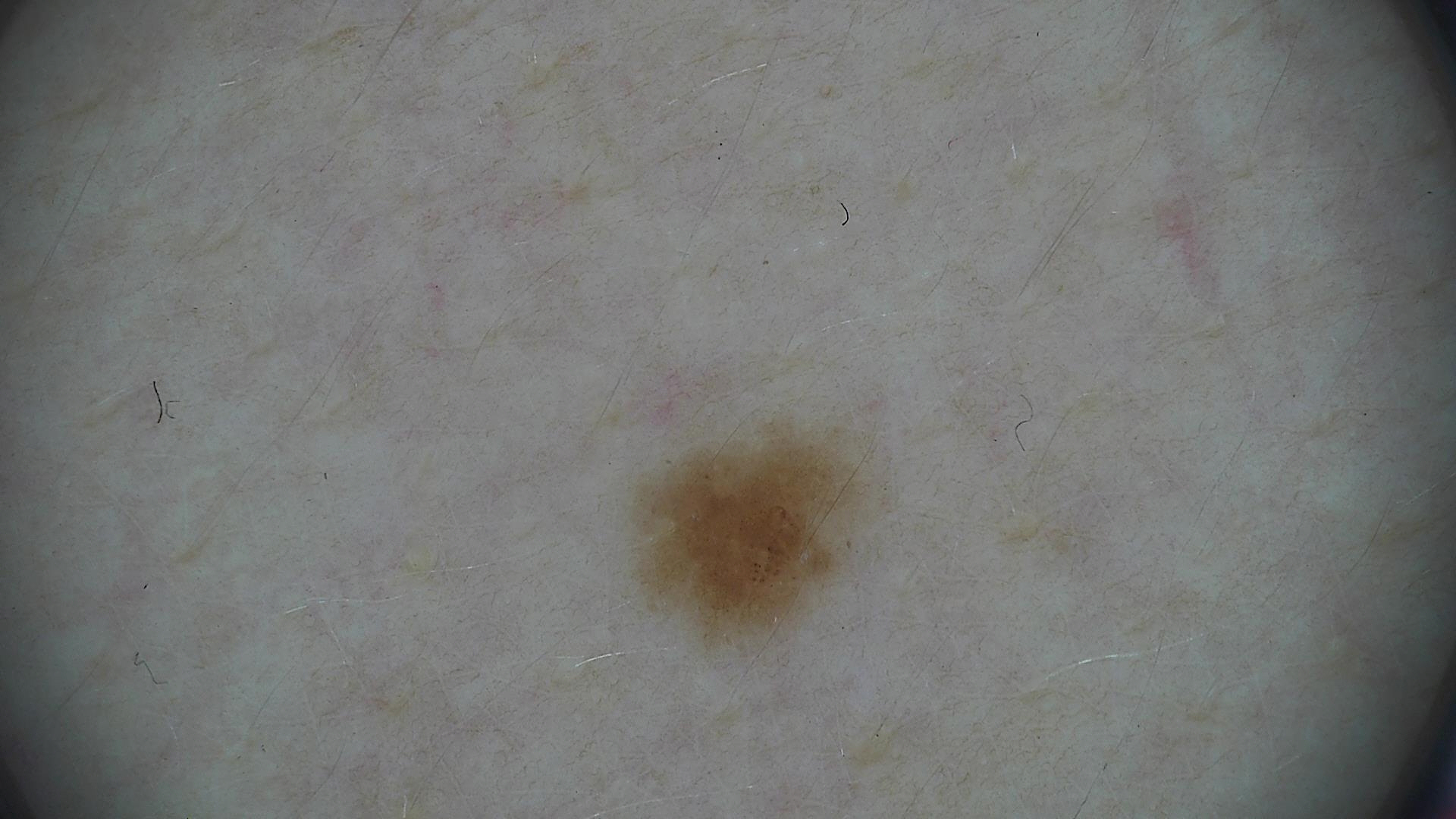Consistent with a dysplastic junctional nevus.